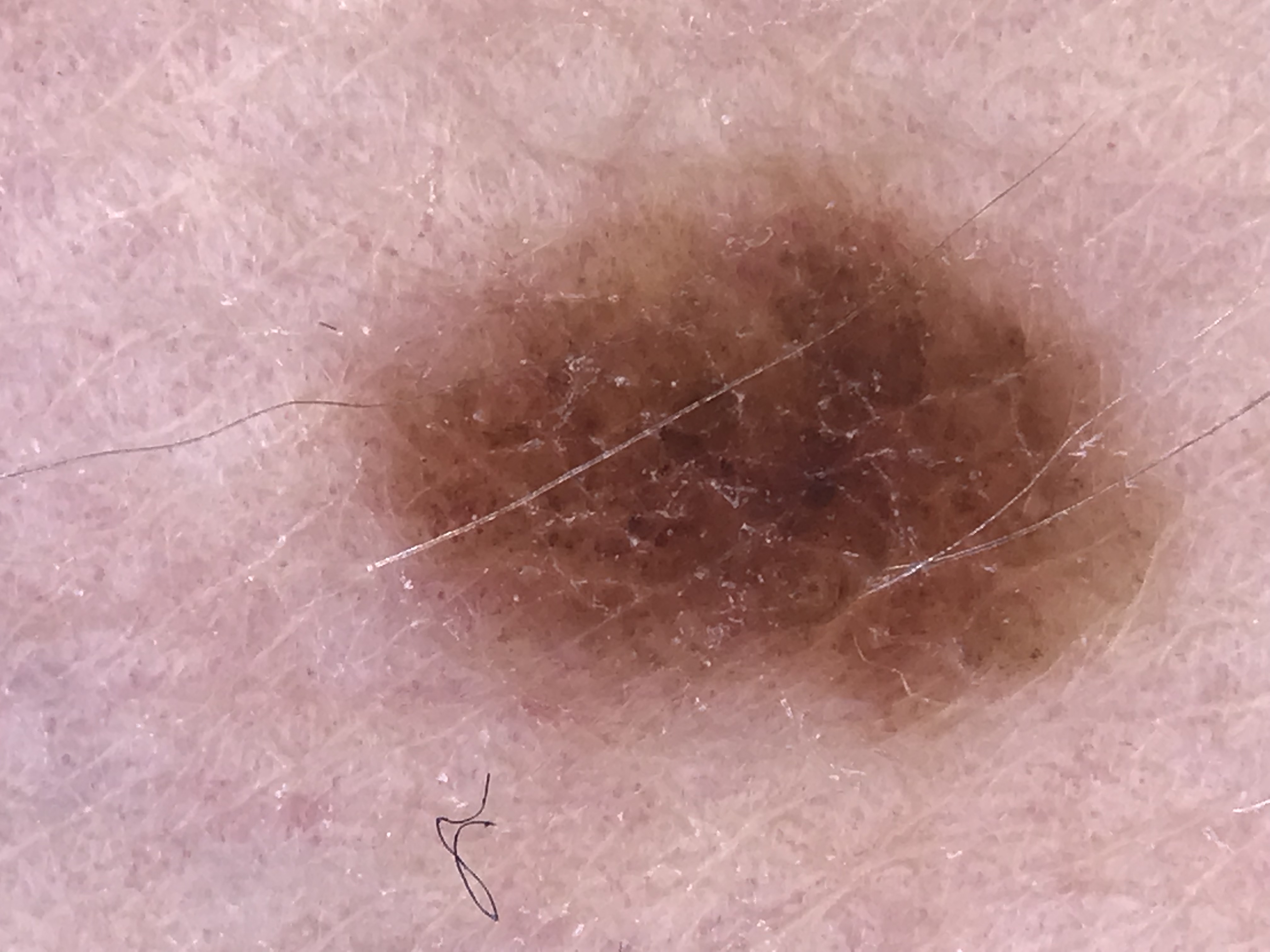A skin lesion imaged with a dermatoscope.
The diagnosis was a benign lesion — a dysplastic compound nevus.